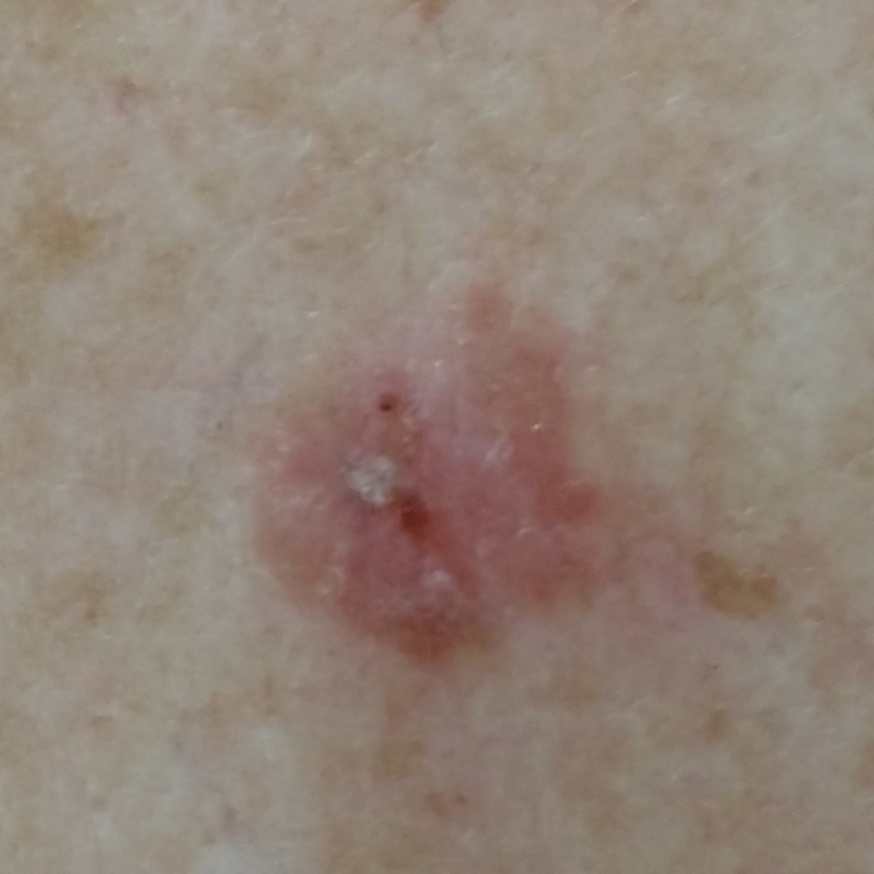diagnosis:
  name: squamous cell carcinoma
  code: SCC
  malignancy: malignant
  confirmation: histopathology